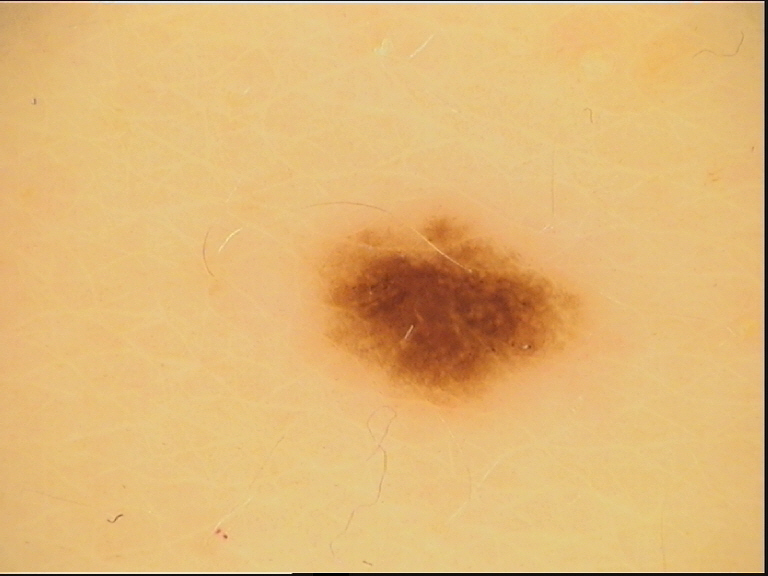Conclusion: Diagnosed as a dysplastic junctional nevus.